A dermoscopic photograph of a skin lesion:
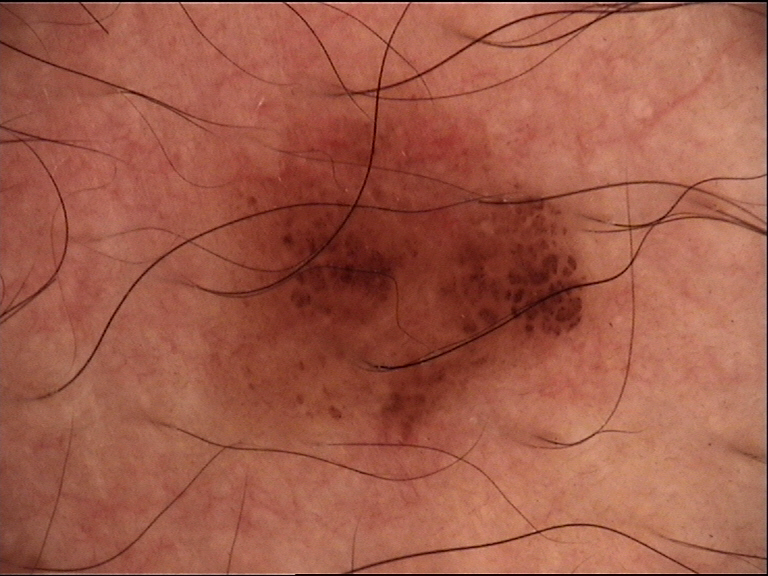The diagnostic label was a banal lesion — a compound nevus.